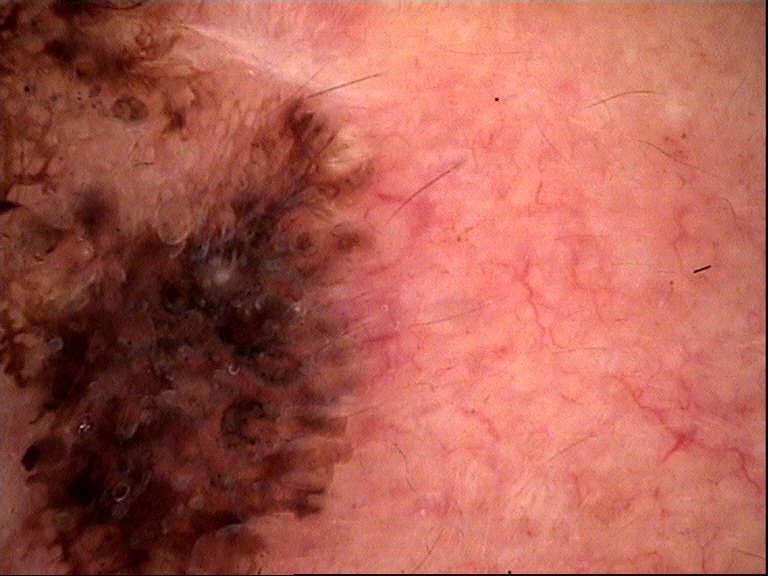Dermoscopy of a skin lesion.
The architecture is that of a keratinocytic lesion.
Consistent with a seborrheic keratosis.